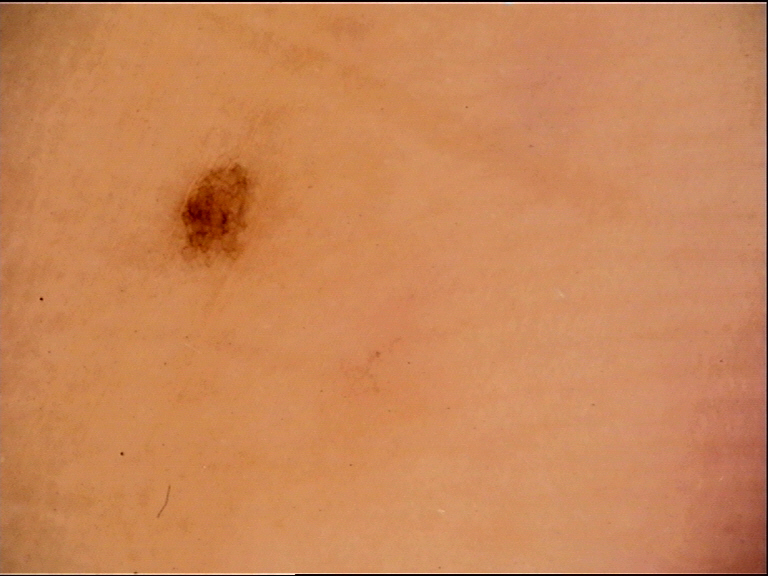{
  "image": "dermatoscopy",
  "diagnosis": {
    "name": "acral dysplastic junctional nevus",
    "code": "ajd",
    "malignancy": "benign",
    "super_class": "melanocytic",
    "confirmation": "expert consensus"
  }
}